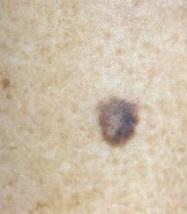Clinical context:
The chart documents a prior melanoma but no melanoma in first-degree relatives. Located on a lower extremity.
Conclusion:
Confirmed on histopathology as a melanoma.